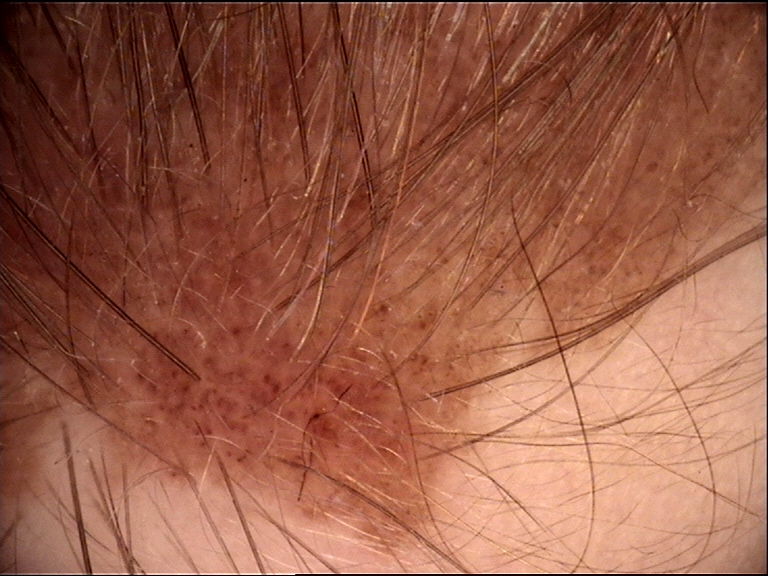A dermoscopic image of a skin lesion. This is a banal lesion. Labeled as a congenital compound nevus.